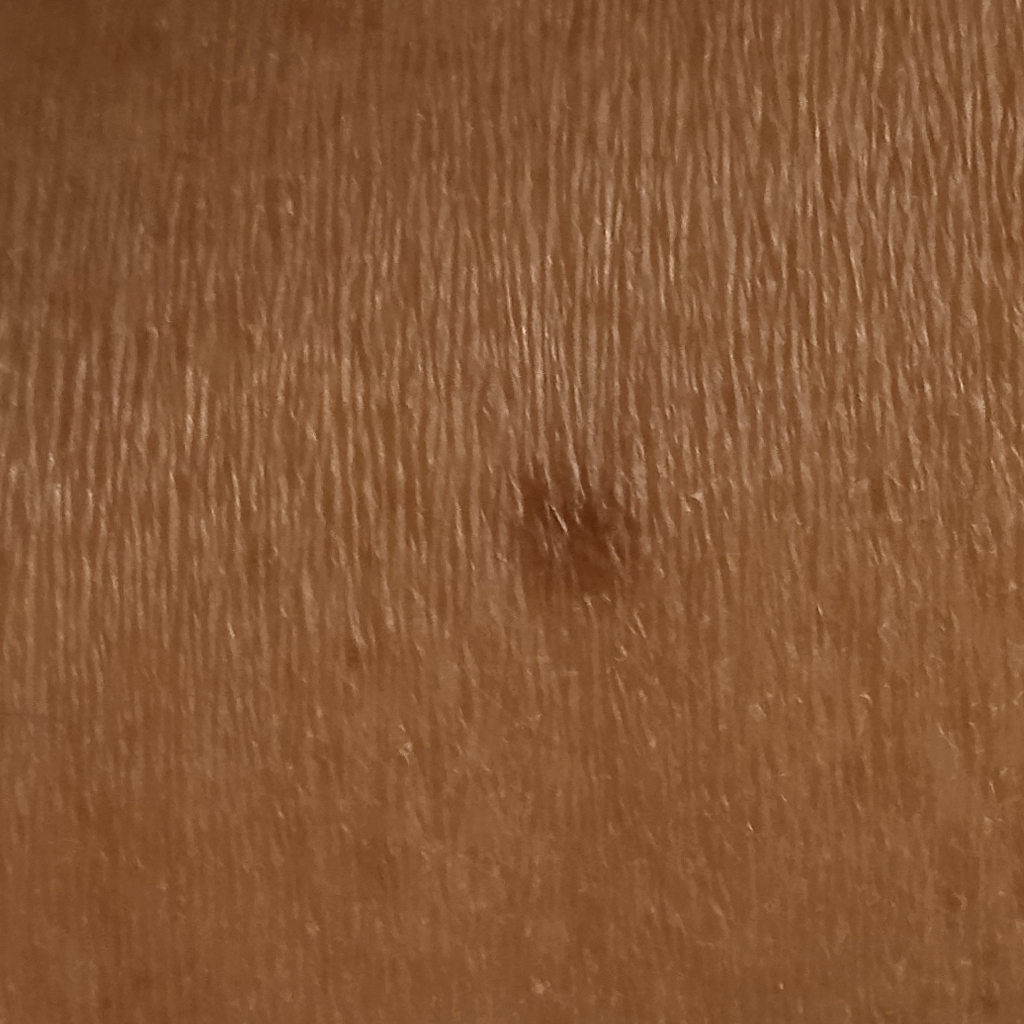referral: research study (no referral diagnosis)
imaging: clinical photograph
patient: female, age 58
body site: a leg
size: 5.2 mm
diagnostic label: dermatofibroma (dermatologist consensus)